A dermoscopic photograph of a skin lesion:
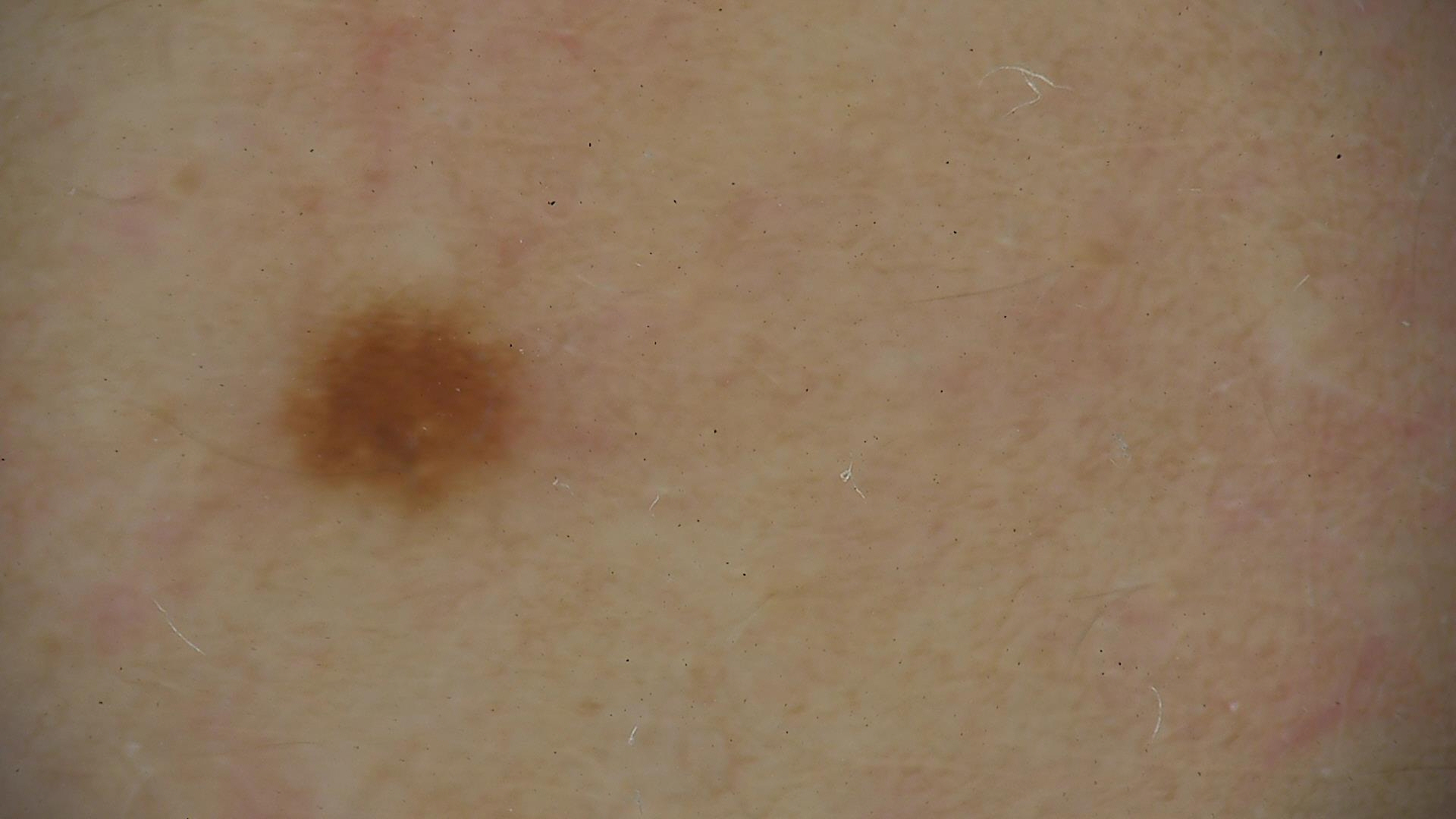Consistent with a dysplastic junctional nevus.